A dermatoscopic image of a skin lesion.
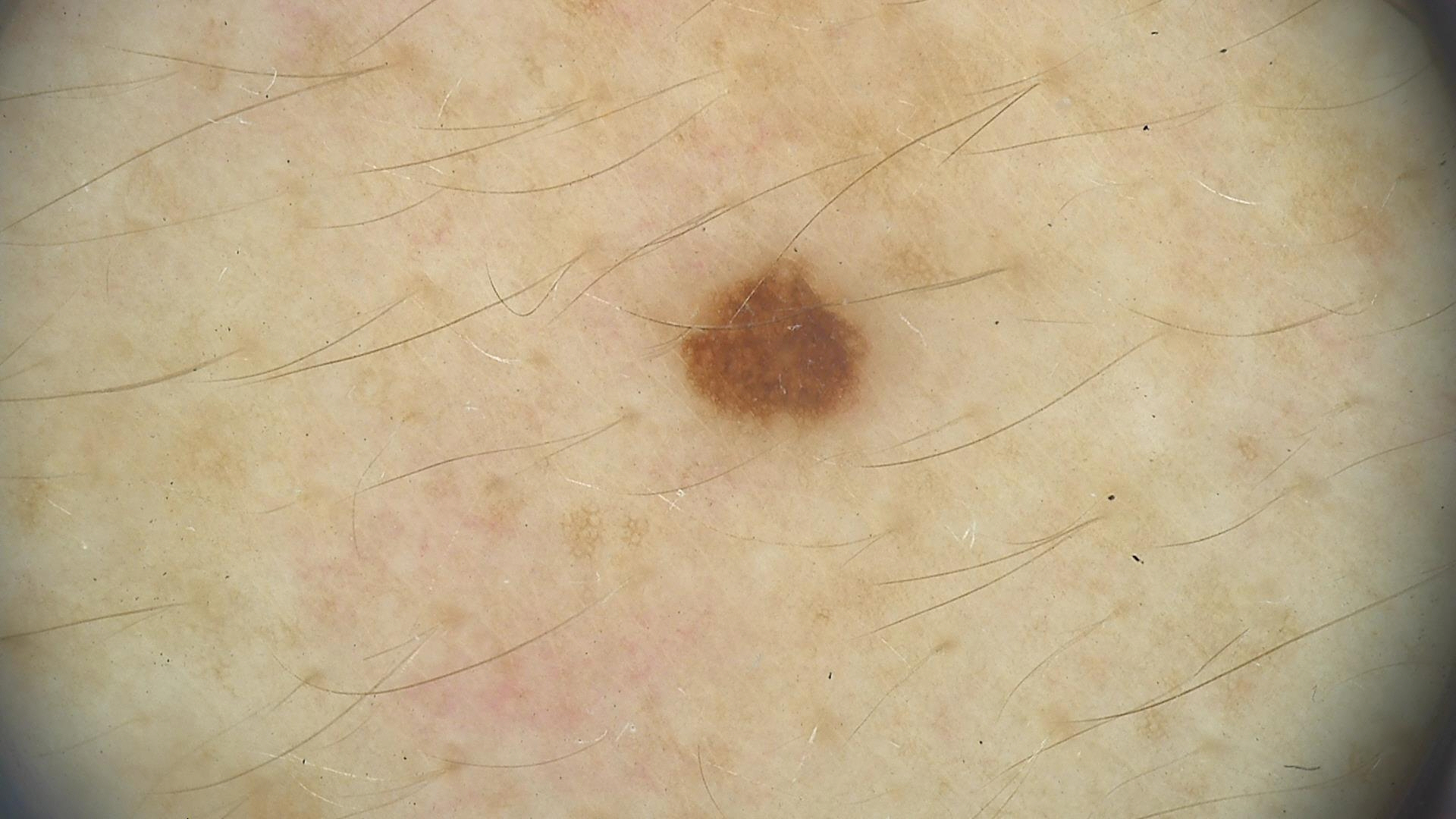Q: What is this lesion?
A: dysplastic junctional nevus (expert consensus)